A dermoscopy image of a single skin lesion. The subject is a male aged 68-72.
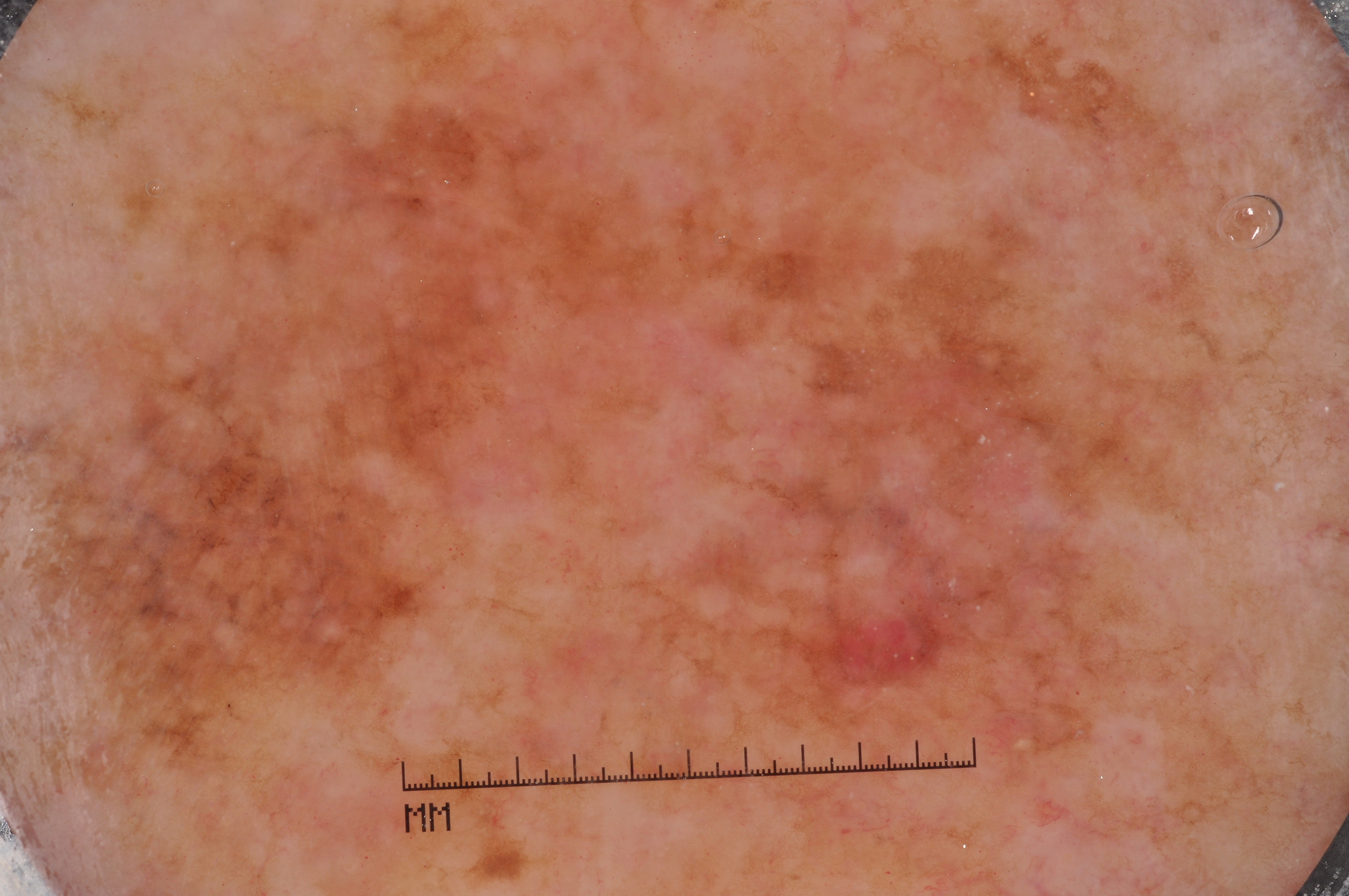dermoscopic pattern: milia-like cysts and pigment network
lesion extent: extends across the entire field of view
assessment: a melanoma, a skin cancer